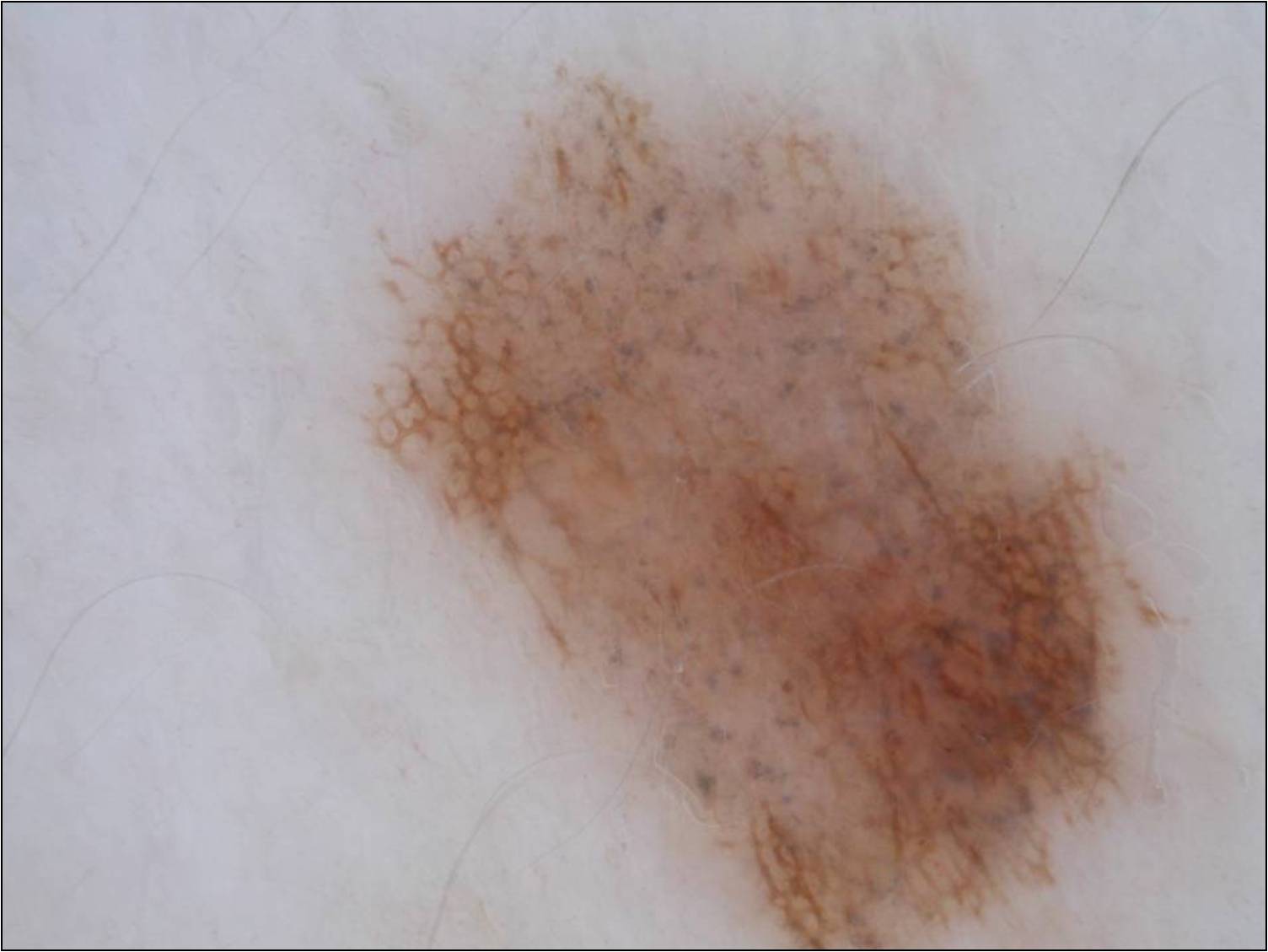Image and clinical context: A dermoscopic image of a skin lesion. A female patient, aged around 40. With coordinates (x1, y1, x2, y2), the lesion is bounded by box(359, 65, 1238, 948). Dermoscopic examination shows pigment network and globules; no negative network, milia-like cysts, or streaks. Impression: Consistent with a melanocytic nevus, a benign lesion.